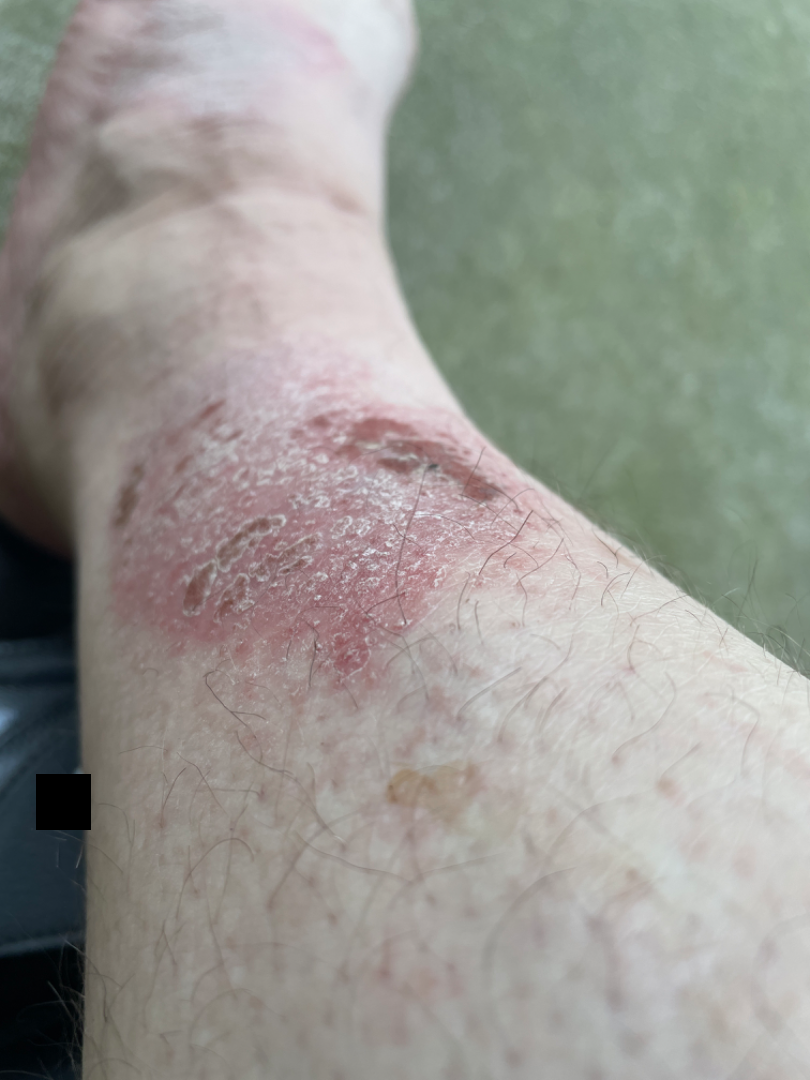Texture is reported as rough or flaky. The patient considered this a rash. Skin tone: Fitzpatrick phototype III. Present for more than one year. The lesion involves the top or side of the foot and leg. The patient is 30–39, male. The photograph was taken at an angle. Reported lesion symptoms include itching. One reviewing dermatologist: the impression was split between Eczema, Impetigo and Allergic Contact Dermatitis.